This image was taken at a distance: 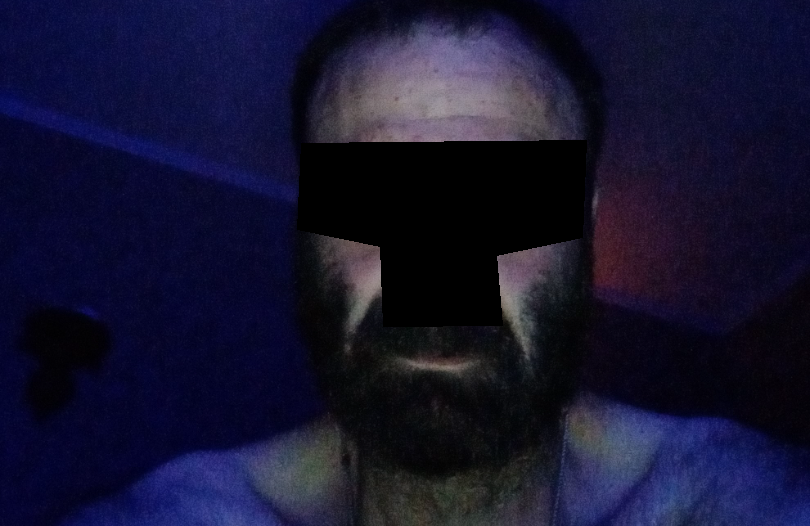{"assessment": "not assessable", "skin_tone": {"monk_skin_tone": [2, 3]}, "texture": "flat"}